The affected area is the arm; this image was taken at a distance; the patient is female: 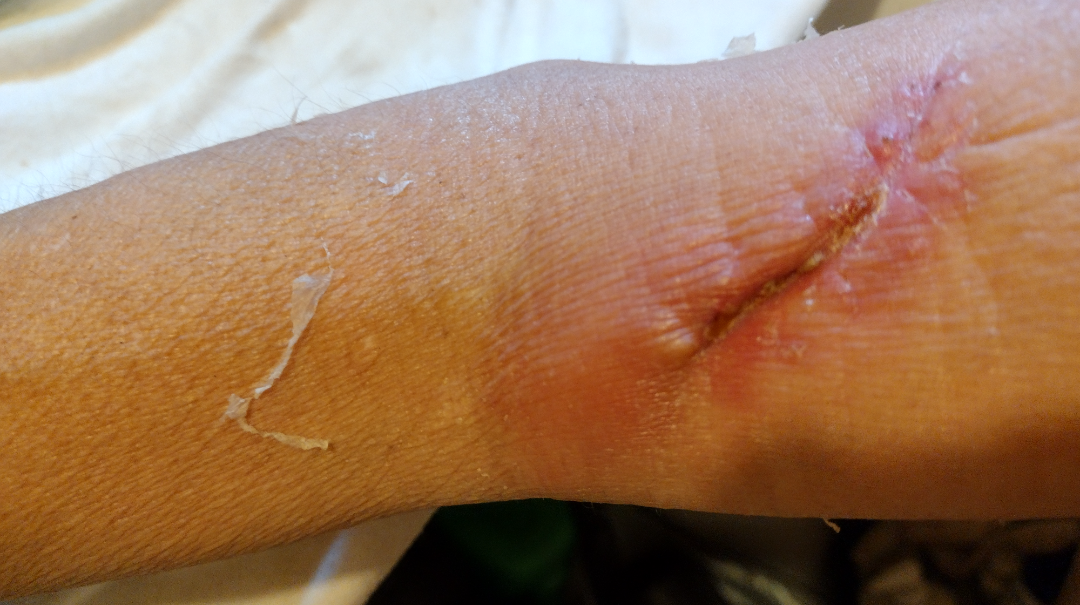Skin tone: Fitzpatrick IV; human graders estimated Monk skin tone scale 3–4. The patient considered this a rash. The patient indicates the condition has been present for one to three months. Texture is reported as raised or bumpy. On photographic review, most consistent with Local infection of wound.